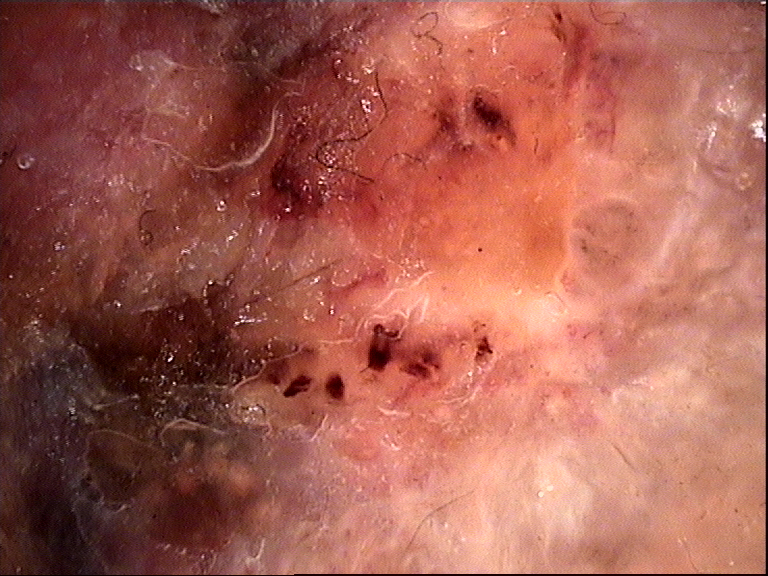<case>
  <image>dermatoscopy</image>
  <lesion_type>
    <main_class>keratinocytic</main_class>
  </lesion_type>
  <diagnosis>
    <name>basal cell carcinoma</name>
    <code>bcc</code>
    <malignancy>malignant</malignancy>
    <super_class>non-melanocytic</super_class>
    <confirmation>histopathology</confirmation>
  </diagnosis>
</case>